A clinical photograph of a skin lesion · referred for assessment of suspected basal cell carcinoma · a female subject age 64:
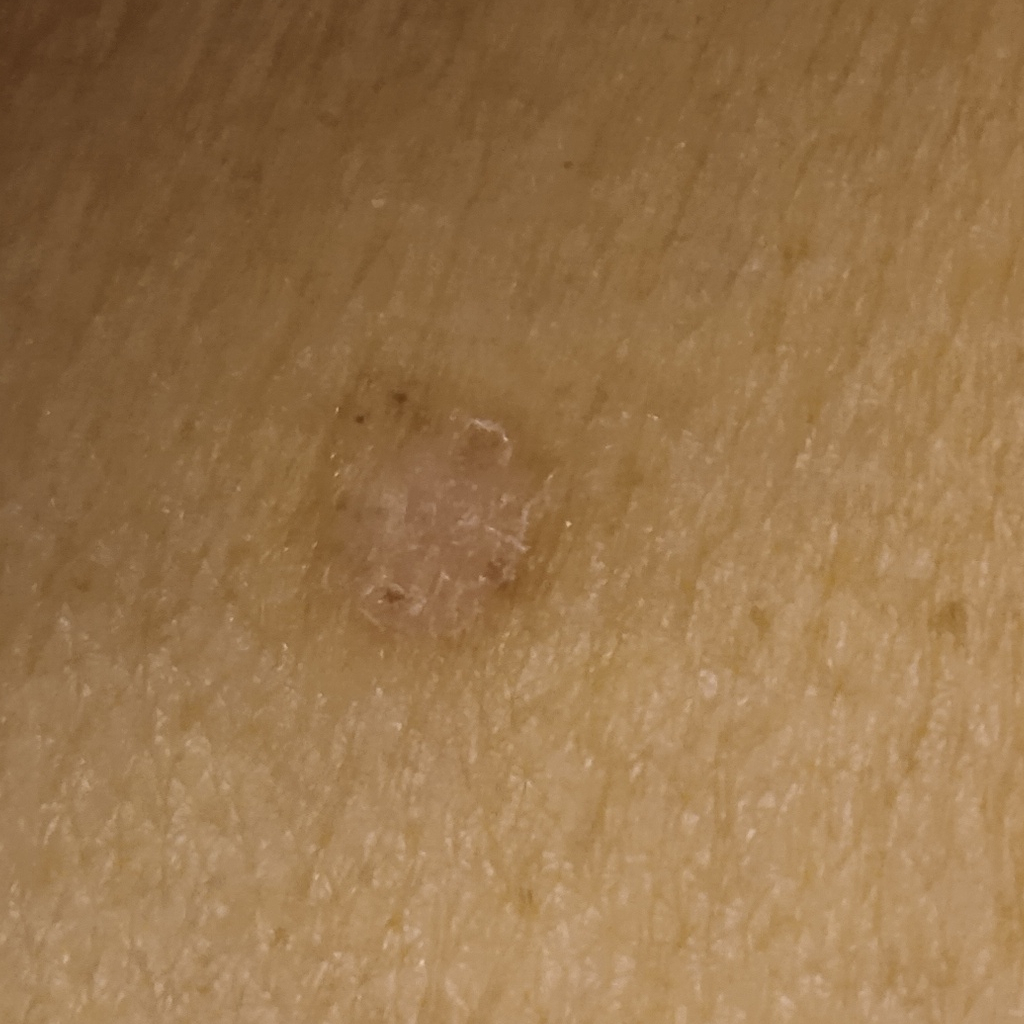The lesion is on the torso.
The lesion measures approximately 8.1 mm.
The biopsy diagnosis was a basal cell carcinoma, following a punch biopsy, with a measured tumor thickness of 0.6 mm.